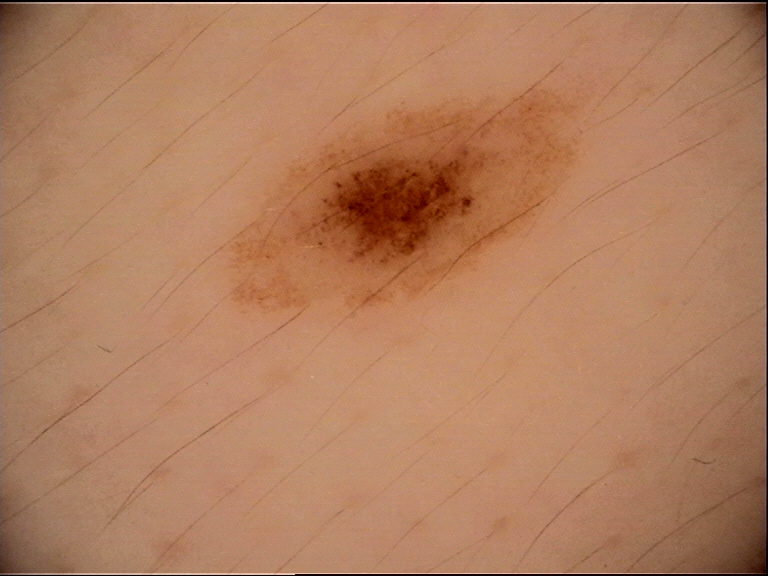A dermoscopic close-up of a skin lesion. Diagnosed as a dysplastic junctional nevus.